A female patient approximately 65 years of age; a skin lesion imaged with contact-polarized dermoscopy: 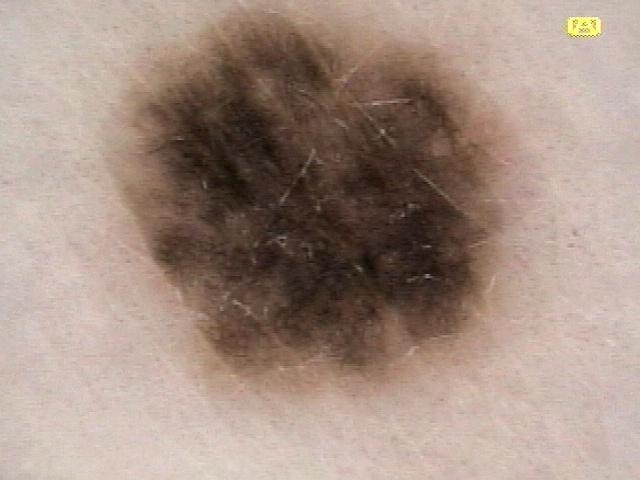The lesion is located on a lower extremity.
Confirmed on histopathology as a nevus.